A dermoscopic close-up of a skin lesion; the patient is a male approximately 10 years of age — 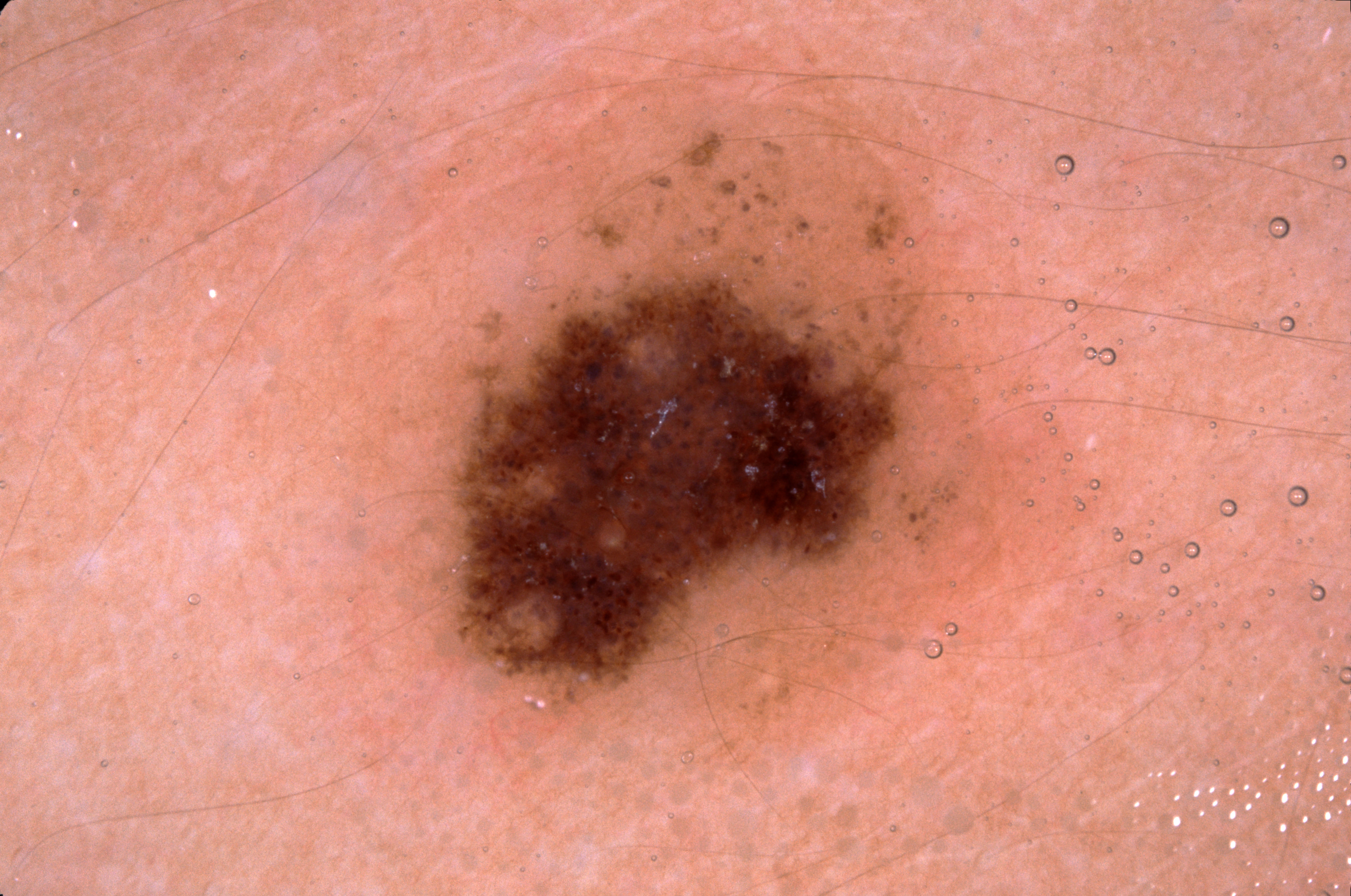| feature | finding |
|---|---|
| dermoscopic features assessed but absent | streaks, milia-like cysts, pigment network, and negative network |
| bounding box | left=351, top=41, right=1111, bottom=771 |
| diagnosis | a melanocytic nevus |